The photo was captured at a distance. The affected area is the arm, back of the hand and front of the torso. Female patient, age 40–49:
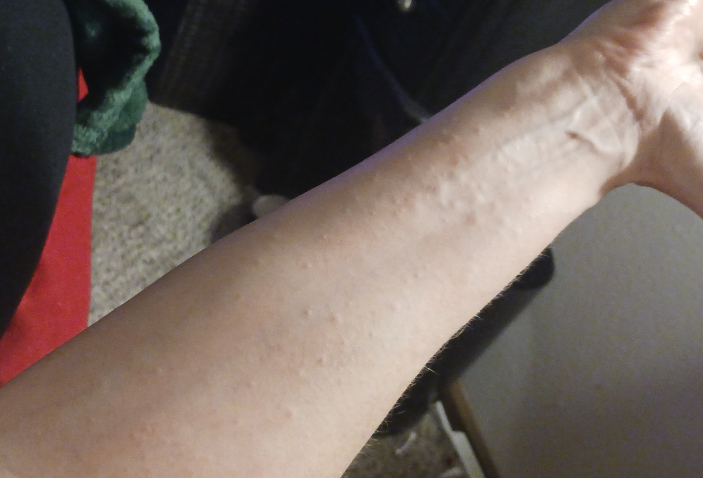patient_category: a rash
skin_tone:
  fitzpatrick: I
  monk_skin_tone:
    - 1
    - 2
duration: less than one week
texture: raised or bumpy
symptoms: itching
differential:
  leading:
    - Contact dermatitis